Female patient, age 18–29; located on the arm; an image taken at a distance — 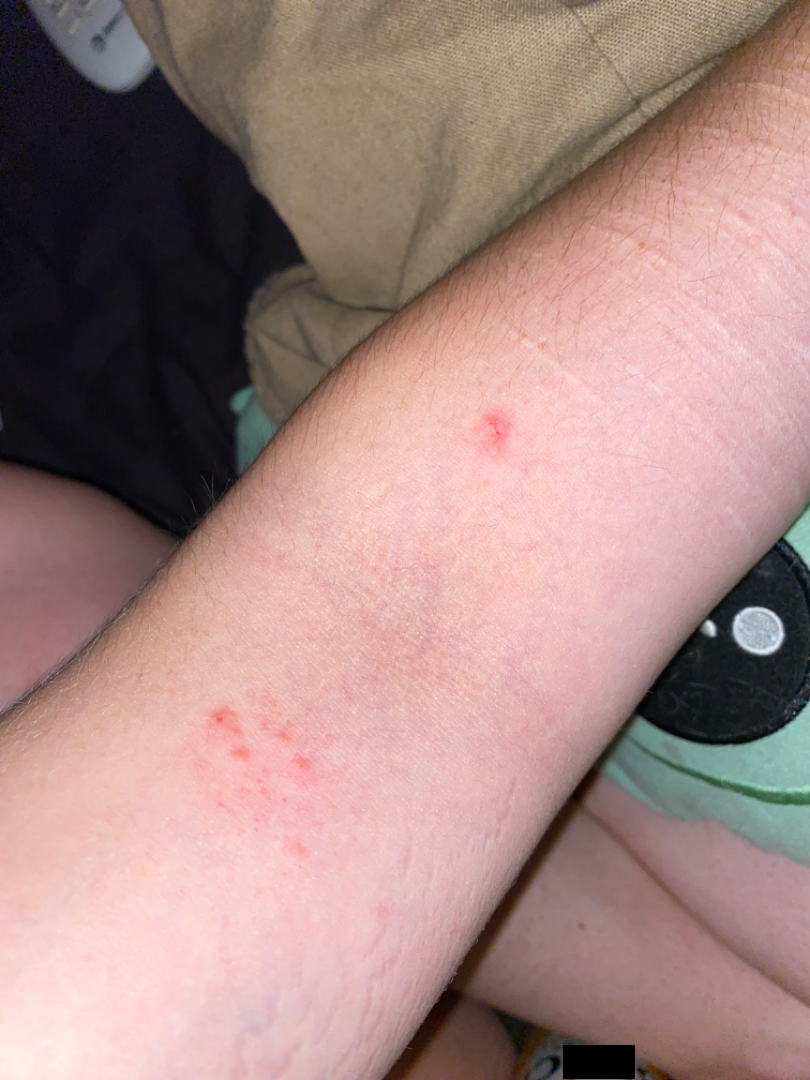{"duration": "less than one week", "texture": ["raised or bumpy", "fluid-filled"], "patient_category": "a rash", "systemic_symptoms": "none reported", "differential": {"tied_lead": ["Allergic Contact Dermatitis", "Acute dermatitis, NOS", "Irritant Contact Dermatitis"], "unlikely": ["Insect Bite", "Eczema"]}}